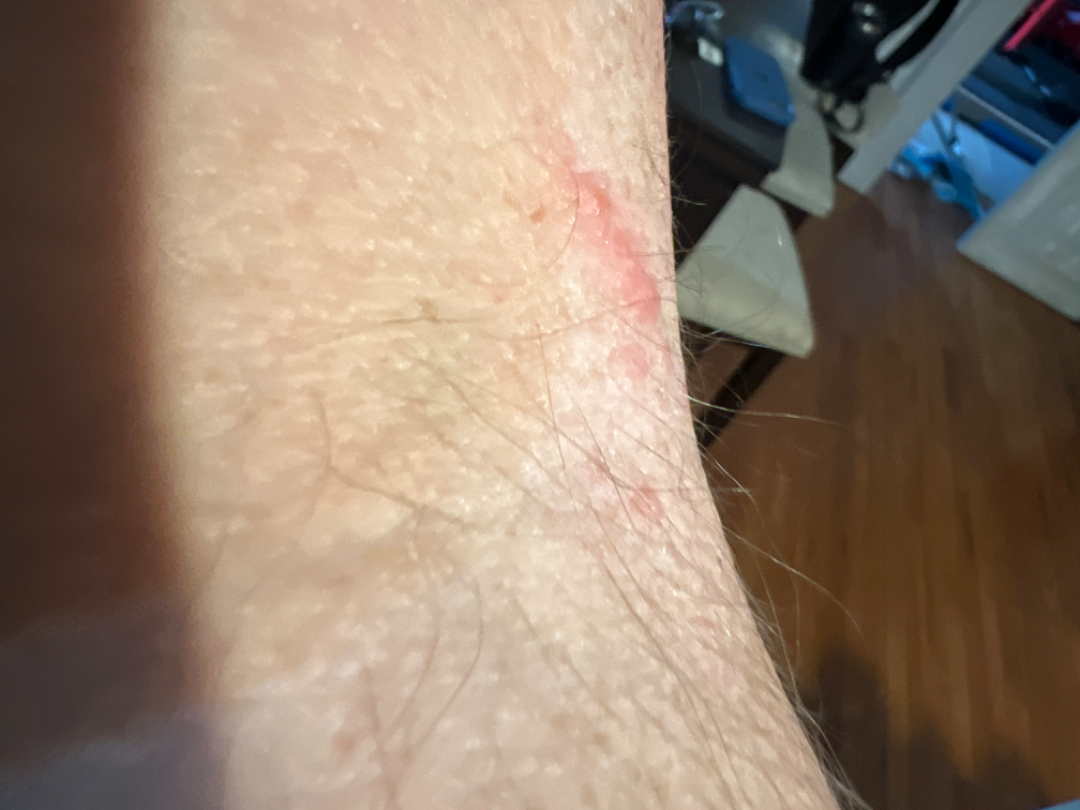lesion symptoms — itching and bothersome appearance | associated systemic symptoms — none reported | surface texture — raised or bumpy | contributor — male, age 40–49 | anatomic site — arm | photo taken — at an angle | present for — one to four weeks | differential — Contact dermatitis (favored); Insect Bite (possible); Allergic Contact Dermatitis (possible); Urticaria (unlikely).